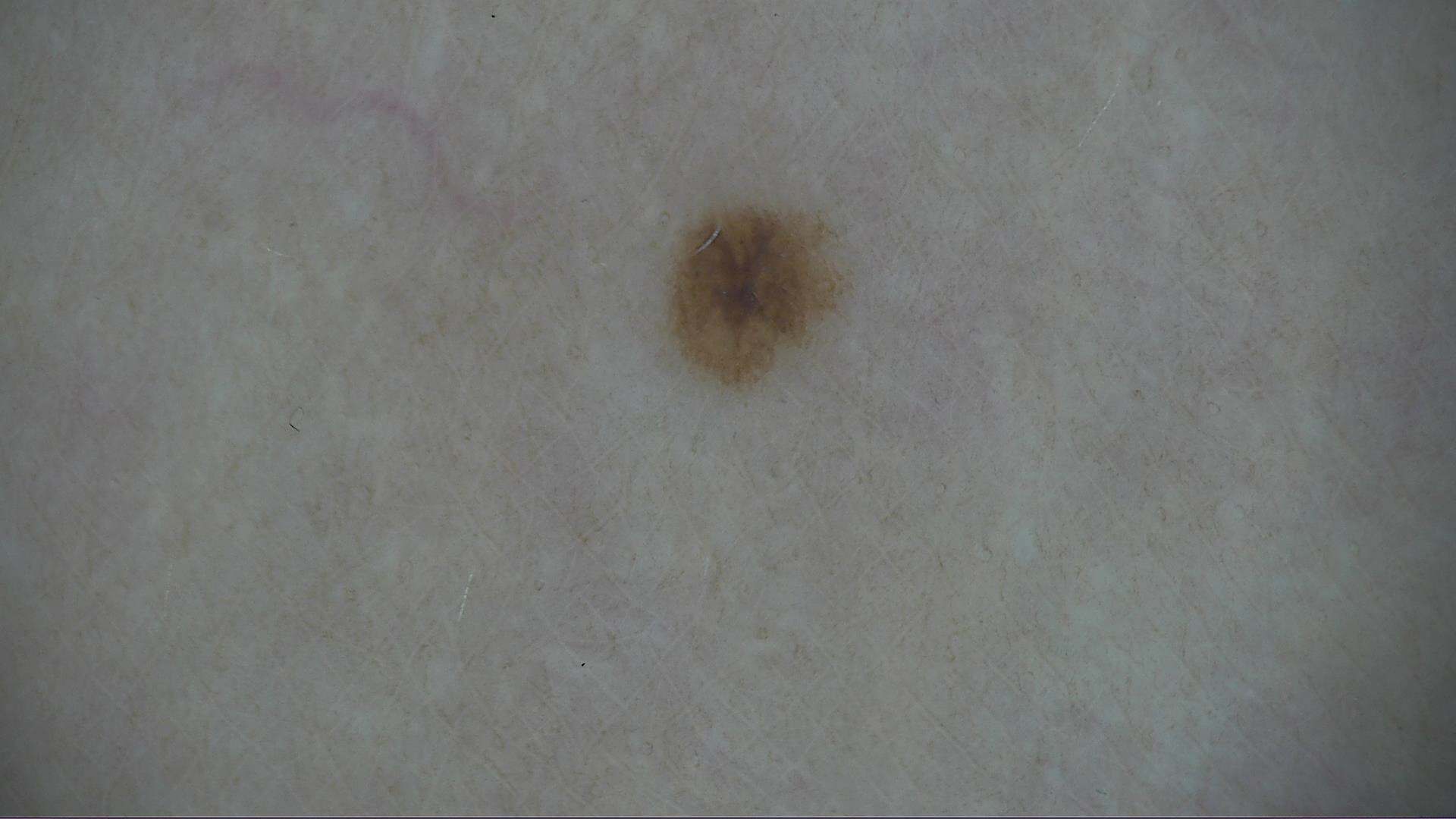Q: What was the diagnostic impression?
A: dysplastic junctional nevus (expert consensus)